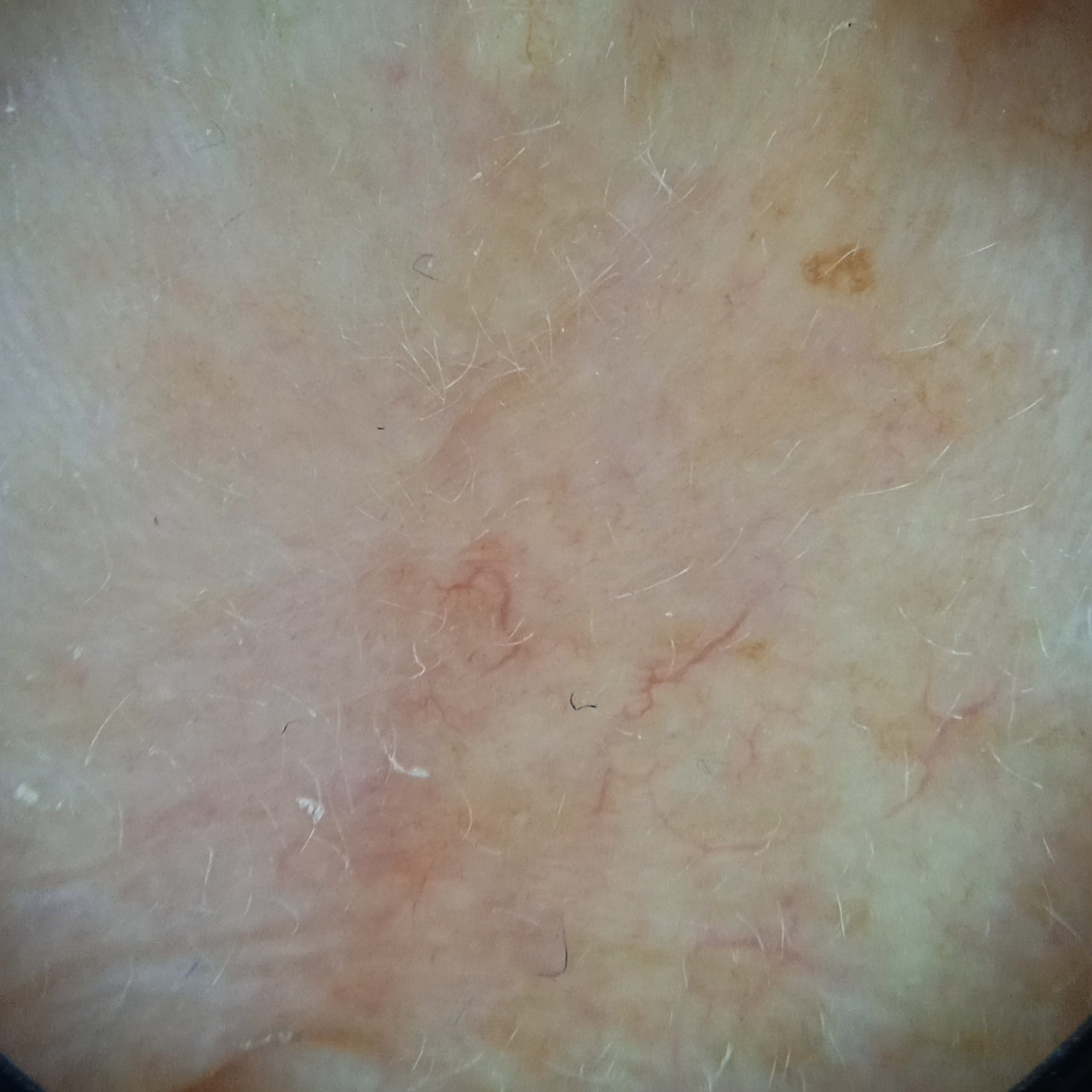Impression:
The consensus diagnosis for this lesion was a basal cell carcinoma.